Dermoscopy of a skin lesion:
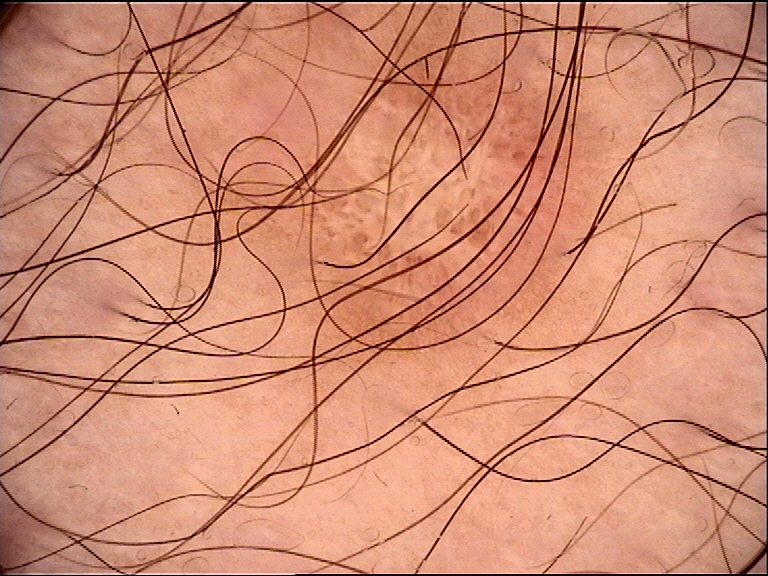Q: What was the diagnostic impression?
A: dermatofibroma (expert consensus)